The patient is 18–29, male. The lesion involves the leg. The photograph is a close-up of the affected area: 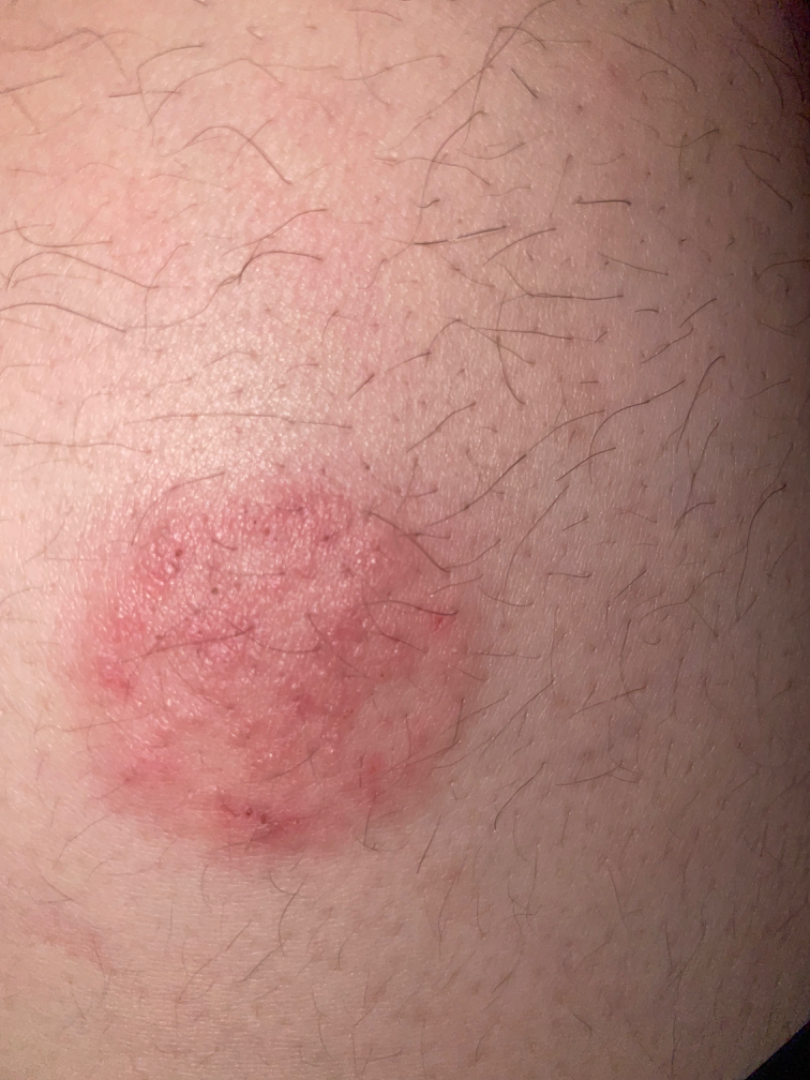Assessment: Three dermatologists independently reviewed the case: the leading consideration is Eczema; also consider Tinea; less probable is Allergic Contact Dermatitis.